A female patient 83 years old; the chart records no prior malignancy (patient or family) and no tobacco use; a clinical photo of a skin lesion taken with a smartphone — 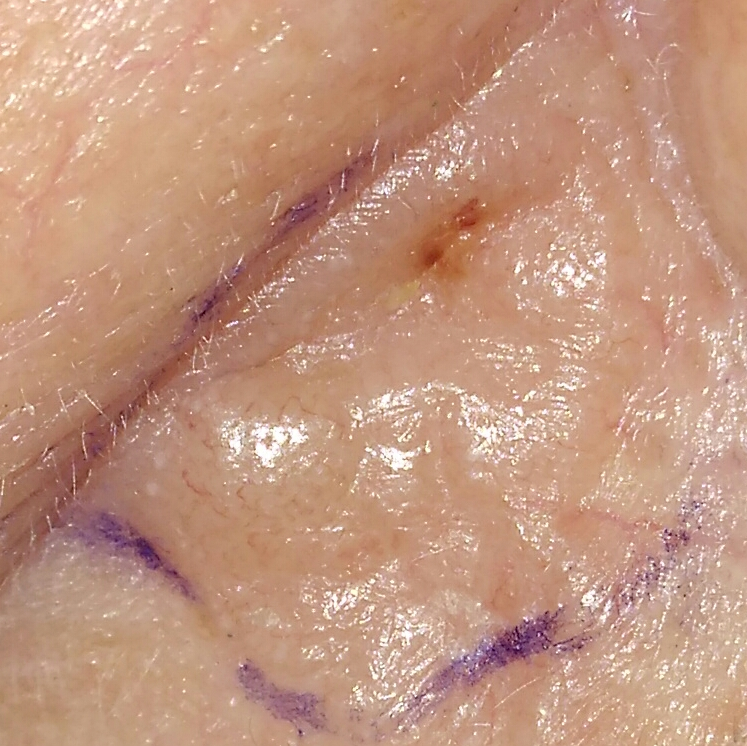site: the face | lesion diameter: approx. 15 × 12 mm | patient-reported symptoms: elevation / no change in appearance, no bleeding | diagnostic label: basal cell carcinoma (biopsy-proven).